Dermoscopy of a skin lesion.
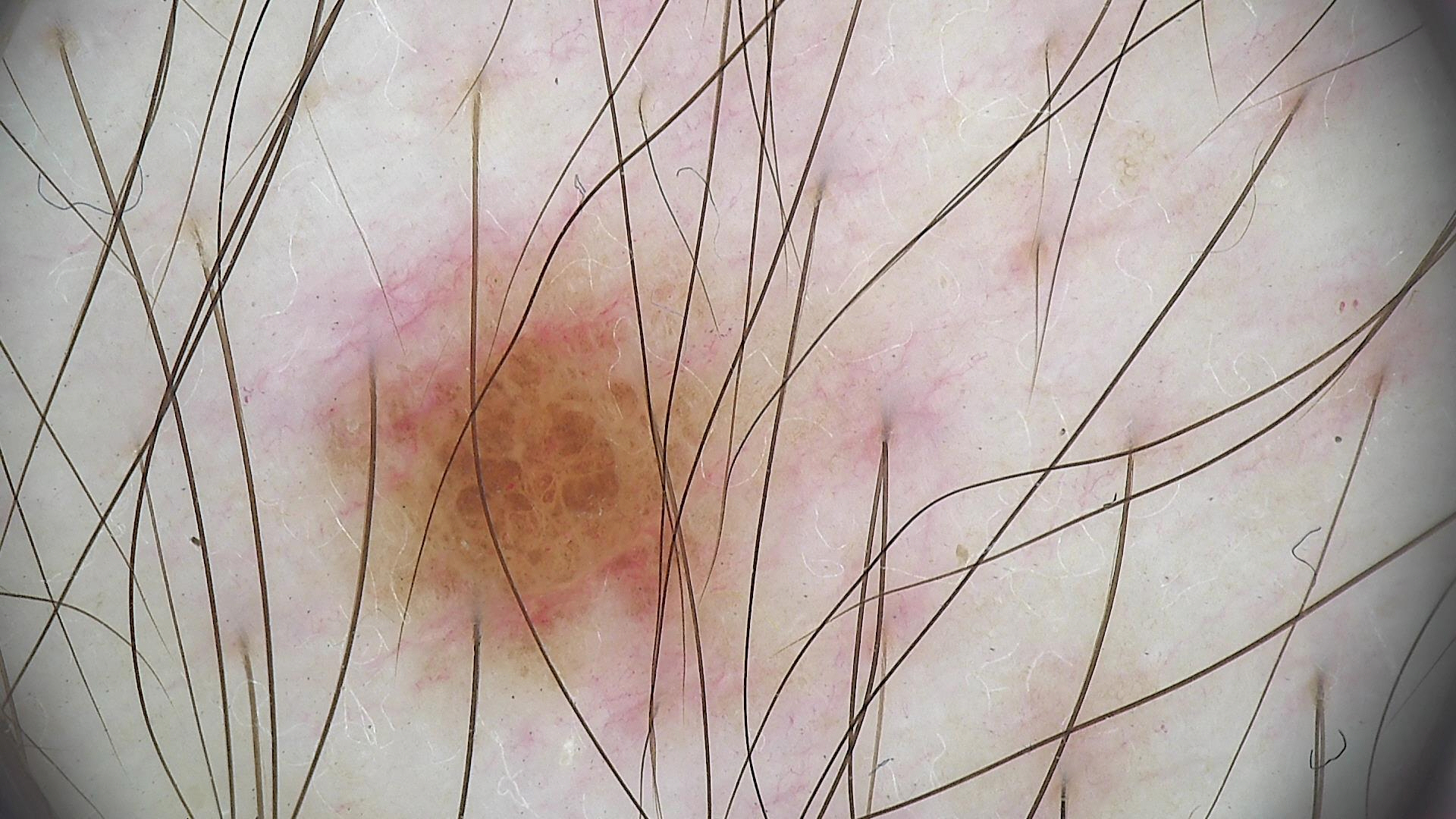Classified as a banal lesion — a compound nevus.